The lesion is described as flat; no relevant systemic symptoms; this image was taken at an angle; self-categorized by the patient as skin that appeared healthy to them; the subject is 18–29, female; the condition has been present for more than one year:
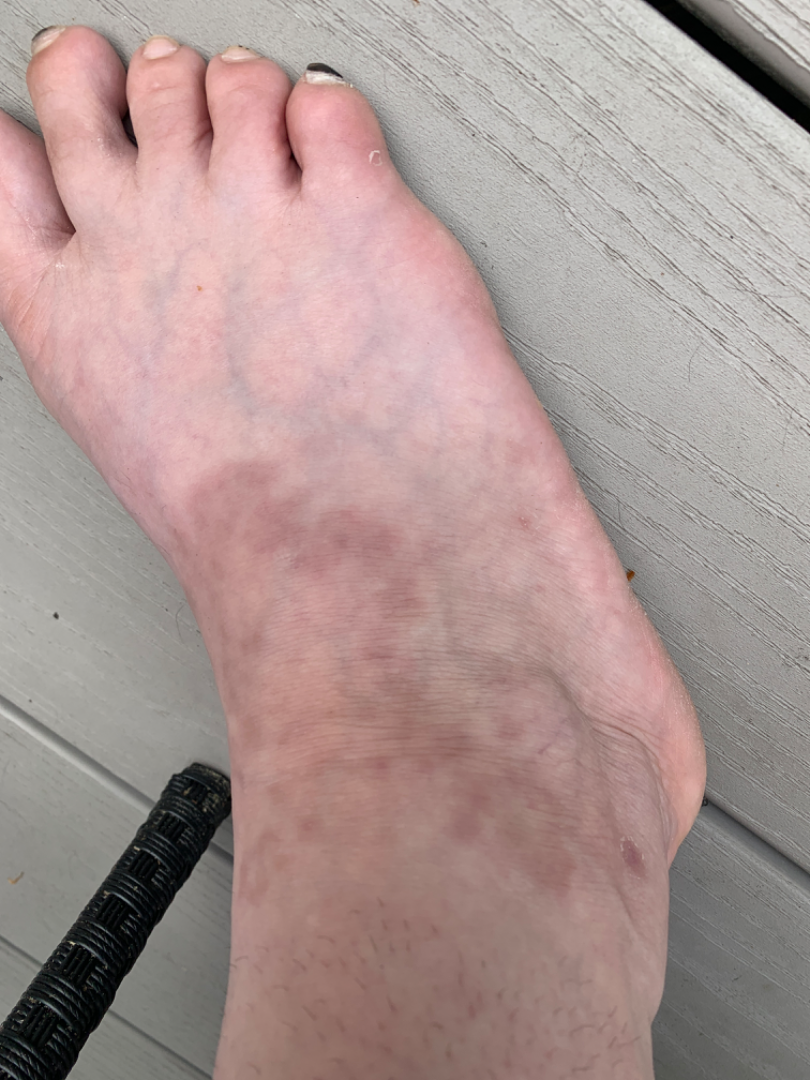Assessment:
On dermatologist assessment of the image, the impression was split between Granuloma annulare, Livedo reticularis and Contact dermatitis; a remote consideration is Stasis Dermatitis.